Close-up view, the lesion involves the arm — 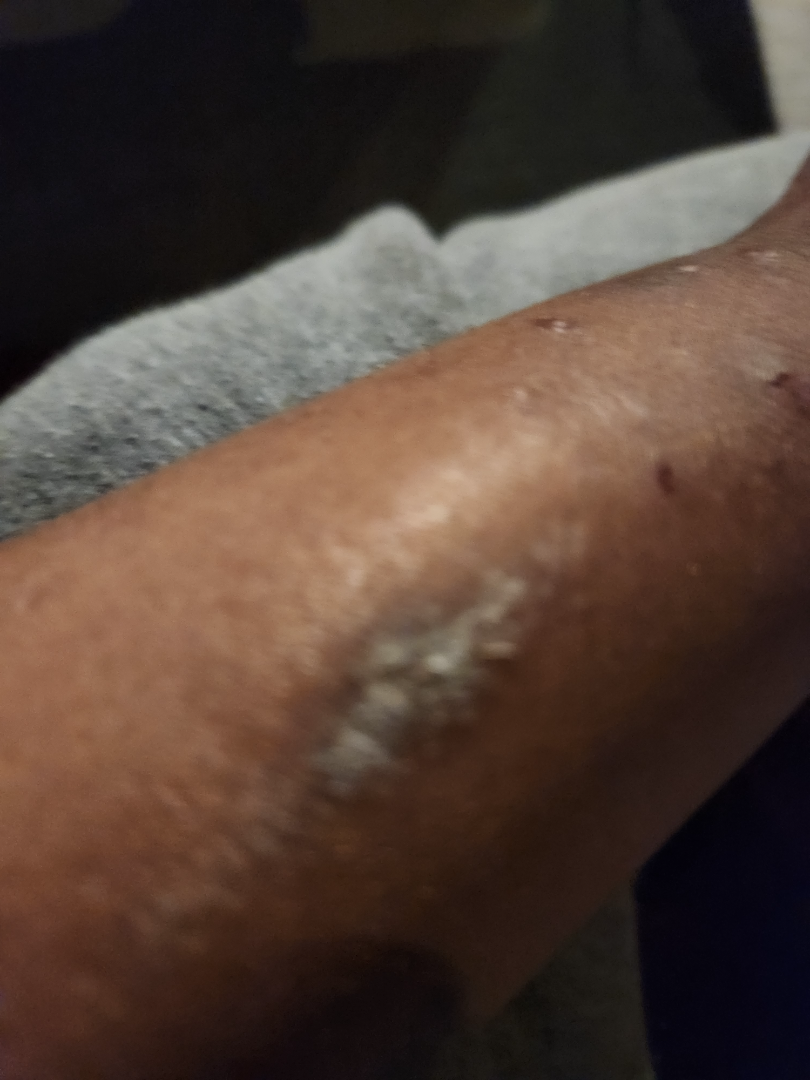No differential diagnosis could be assigned on photographic review. The contributor notes the condition has been present for one to three months. Texture is reported as fluid-filled and raised or bumpy. The lesion is associated with itching.